No relevant systemic symptoms · the lesion involves the top or side of the foot and leg · the patient described the issue as a rash · present for less than one week · symptoms reported: itching · FST II; human graders estimated Monk skin tone scale 2 or 3 · the photograph is a close-up of the affected area: 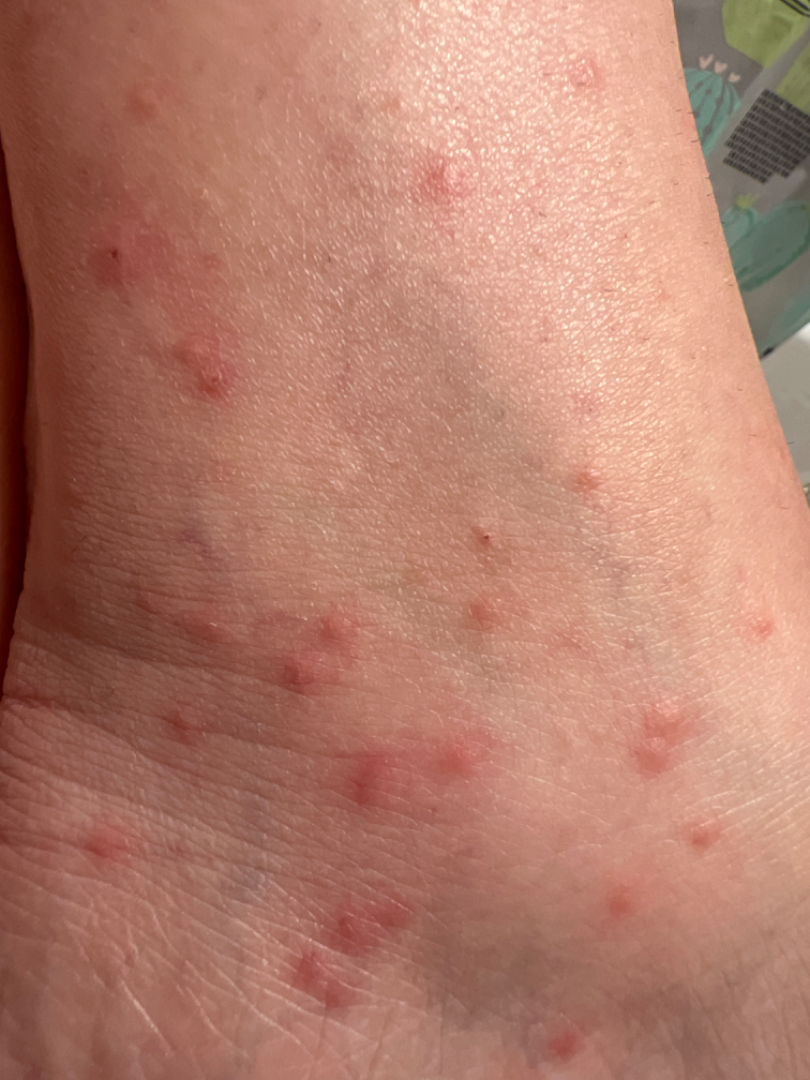differential:
  leading:
    - Scabies
  considered:
    - Insect Bite
  unlikely:
    - Eczema